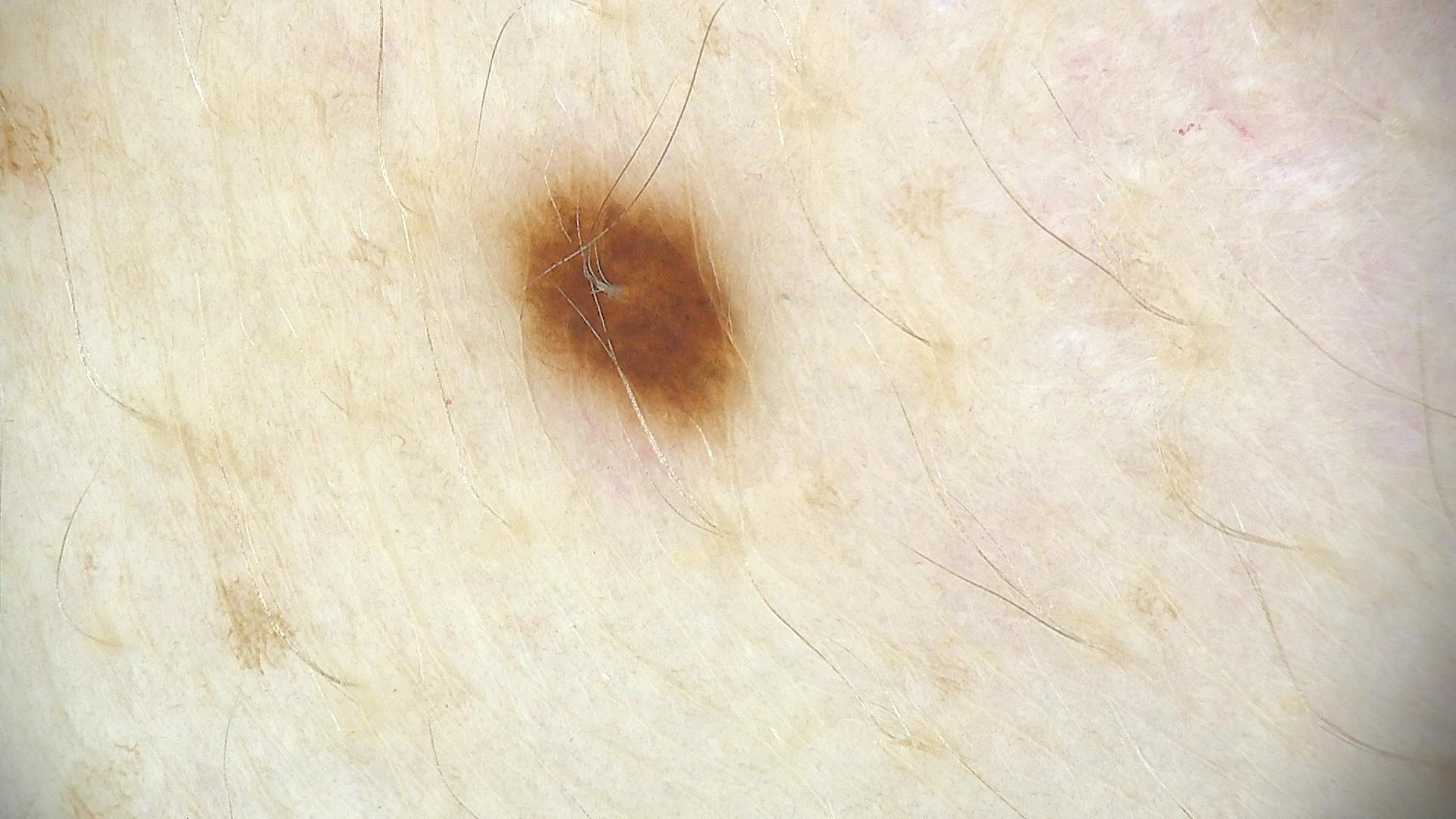Findings:
• diagnosis — dysplastic junctional nevus (expert consensus)